The patient reports itching; this image was taken at an angle; self-categorized by the patient as a rash; the condition has been present for about one day; the patient is 18–29, female; the arm is involved: 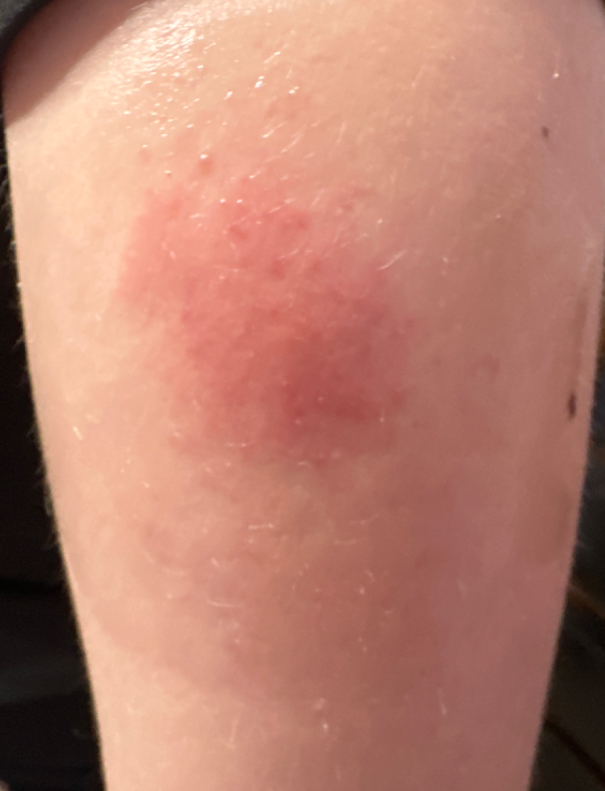clinical impression = the differential includes Impetigo, Injection site disorder and Allergic Contact Dermatitis, with no clear leading consideration.